The photograph was taken at an angle; located on the arm — 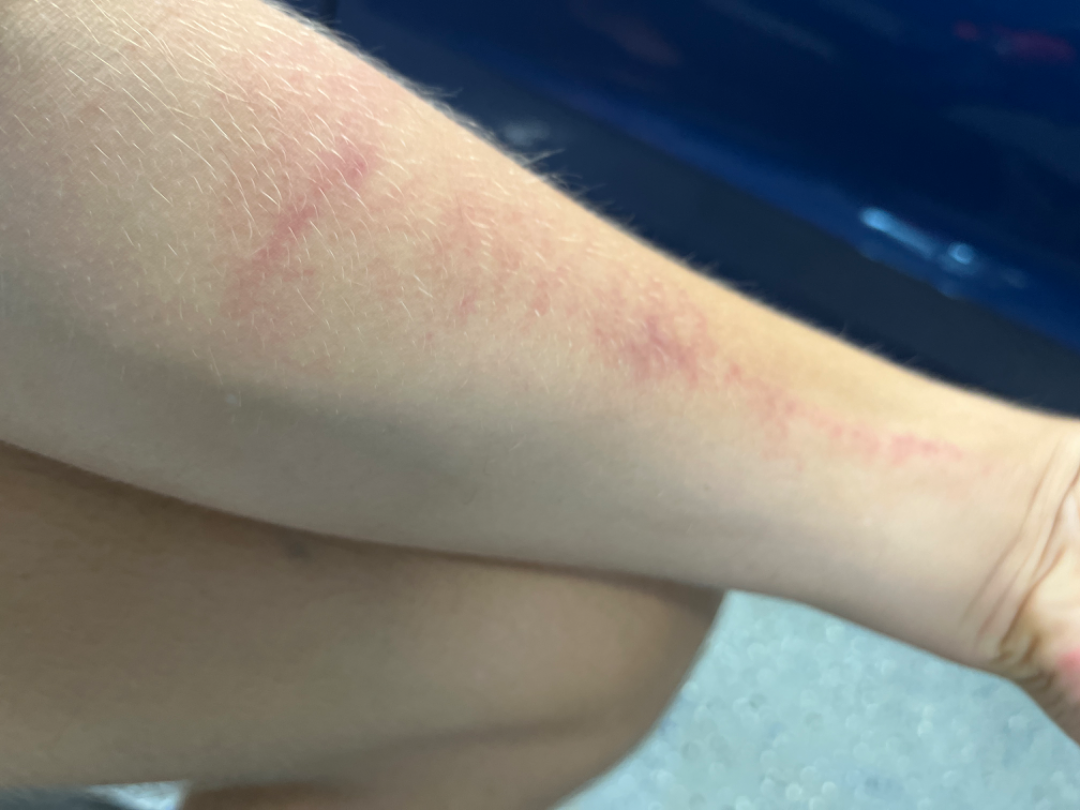  assessment: unable to determine